The patient is a male aged approximately 70. A dermoscopy image of a single skin lesion — 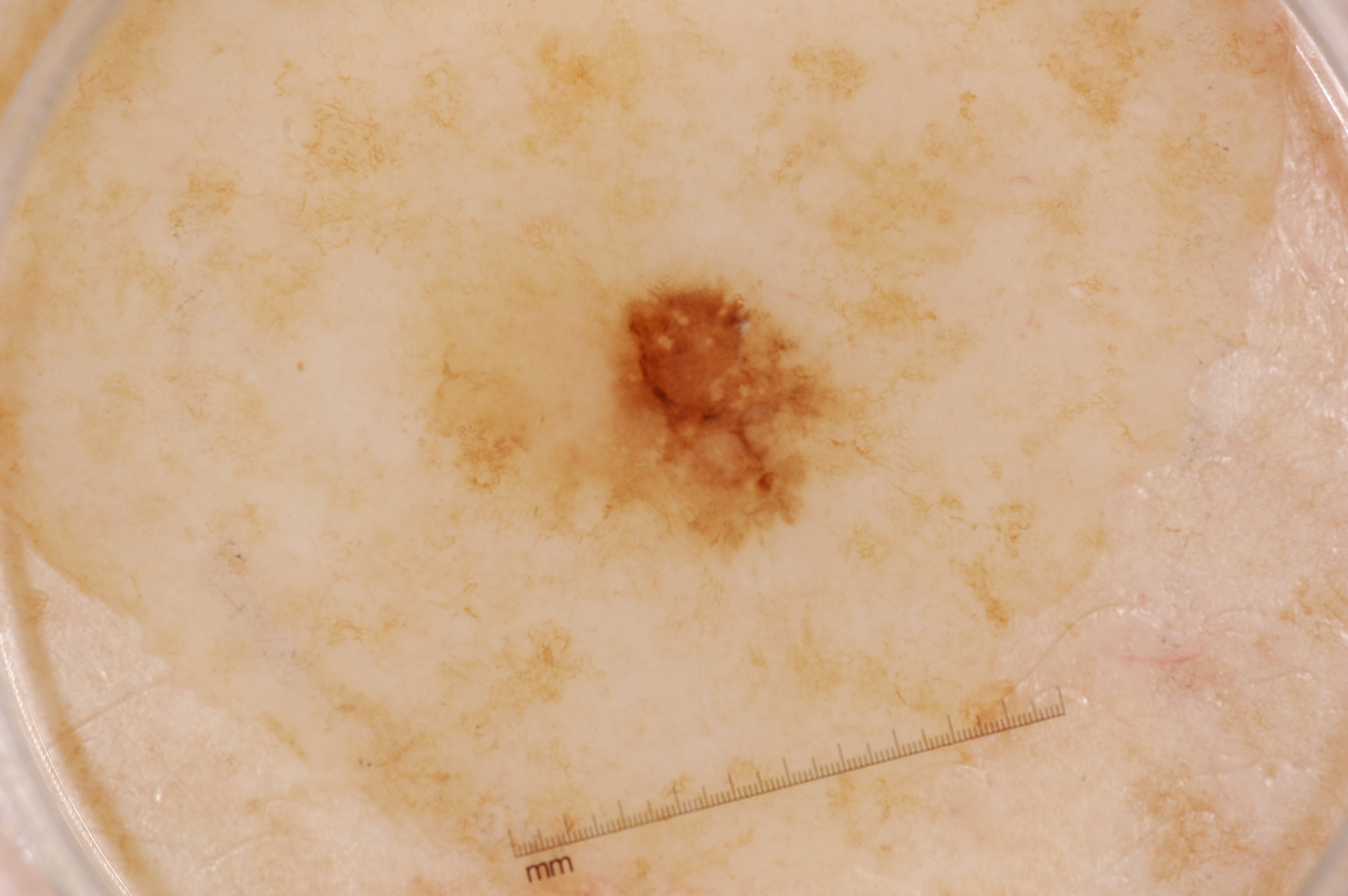{
  "dermoscopic_features": {
    "present": [],
    "absent": [
      "pigment network",
      "negative network",
      "streaks",
      "milia-like cysts"
    ]
  },
  "lesion_extent": "small",
  "lesion_location": {
    "bbox_xyxy": [
      602,
      281,
      837,
      546
    ]
  },
  "diagnosis": {
    "name": "melanoma",
    "malignancy": "malignant",
    "lineage": "melanocytic",
    "provenance": "histopathology"
  }
}